The patient reports the condition has been present for more than five years; the contributor is a female aged 30–39; Fitzpatrick phototype IV; the patient also reports shortness of breath and fatigue; this is a close-up image; texture is reported as raised or bumpy; the patient reports enlargement, bothersome appearance and itching: 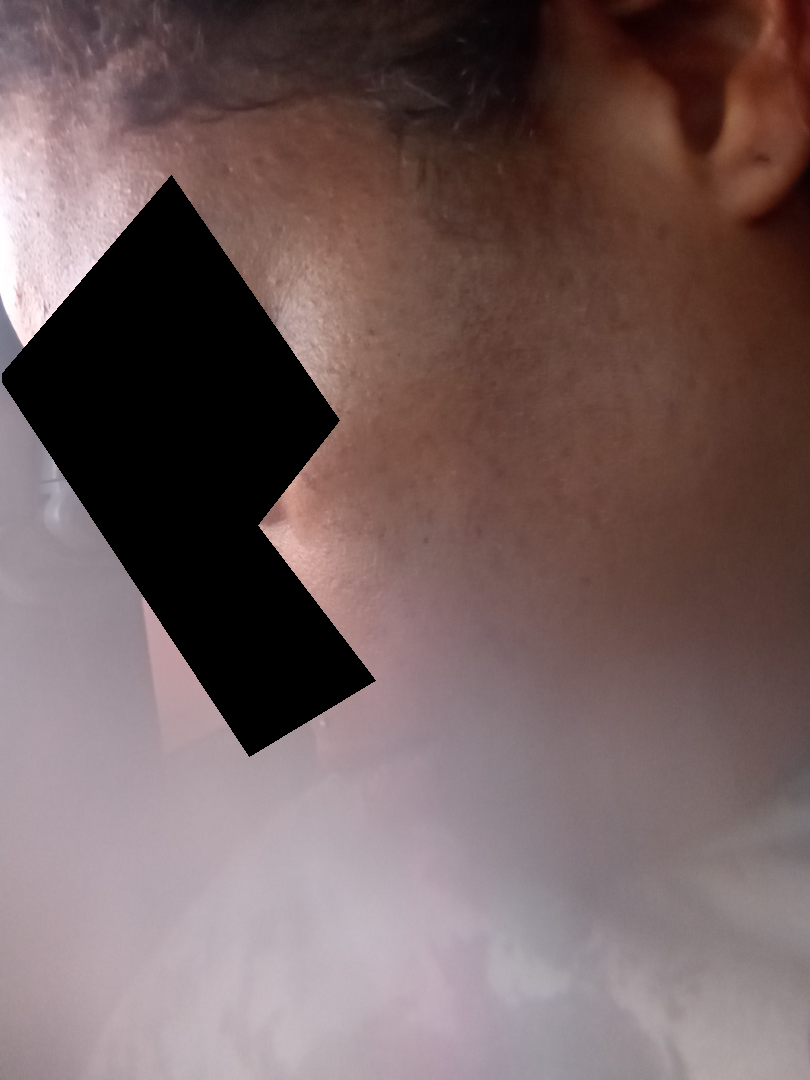Impression:
The skin condition could not be confidently assessed from this image.